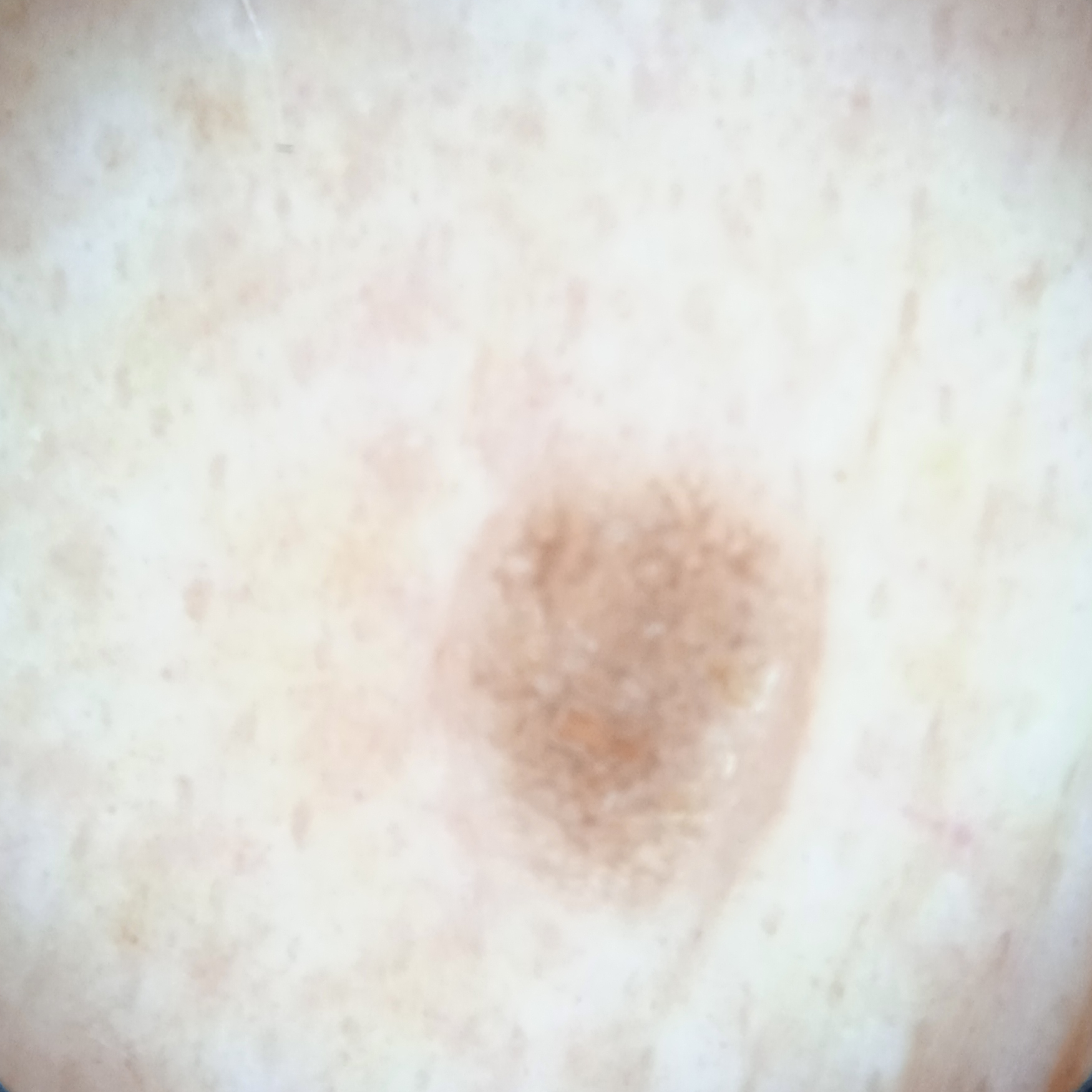{
  "image": "dermatoscopic image",
  "mole_burden": "a moderate number of melanocytic nevi",
  "sun_reaction": "skin reddens painfully with sun exposure",
  "patient": {
    "age": 81,
    "sex": "female"
  },
  "lesion_size": {
    "diameter_mm": 5.3
  },
  "diagnosis": {
    "name": "seborrheic keratosis",
    "malignancy": "benign"
  }
}